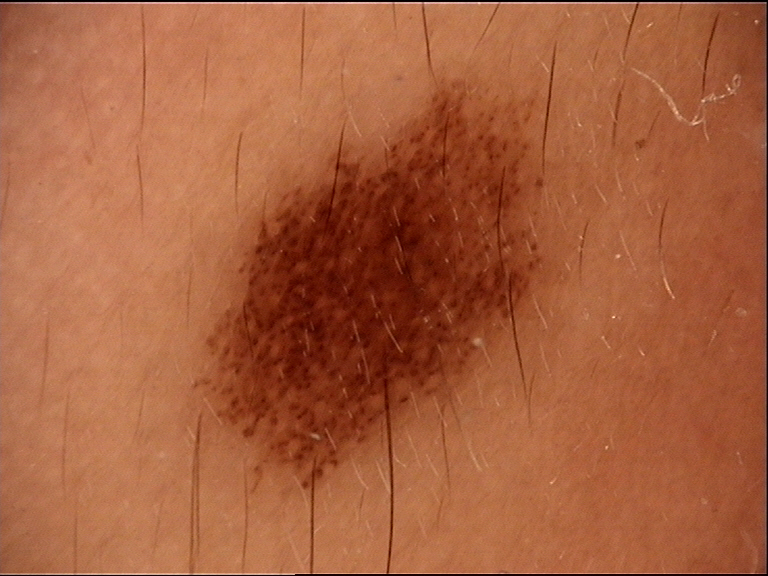The diagnosis was a junctional nevus.